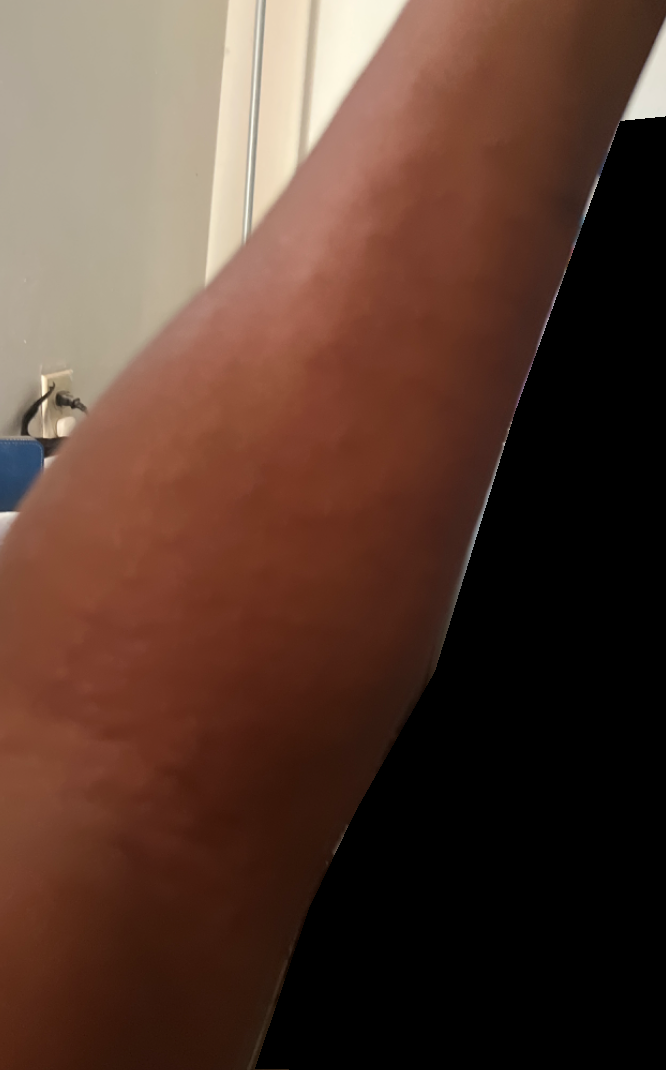The reviewer was unable to grade this case for skin condition. The lesion is described as raised or bumpy. Reported duration is less than one week. The patient is 50–59, female. This is a close-up image. No relevant systemic symptoms. The lesion involves the arm. The patient described the issue as skin that appeared healthy to them.